Few moles overall by the patient's own estimate. The patient says their skin tans without first burning. A dermoscopic image of a skin lesion. A male patient 79 years old. Acquired for a research image collection, with no referral diagnosis — 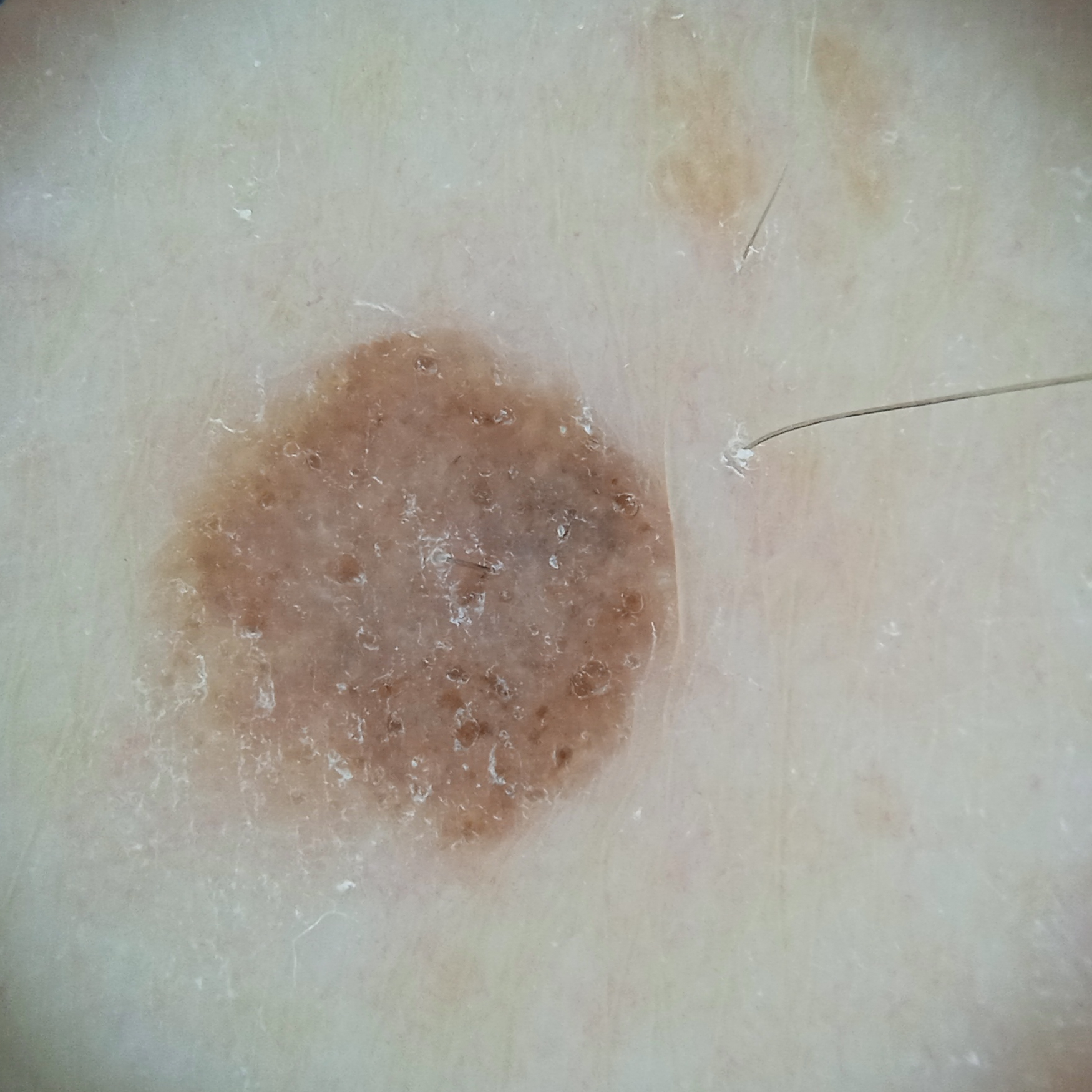Measuring roughly 5.8 mm. The diagnostic impression was a melanocytic nevus.